A dermoscopy image of a single skin lesion.
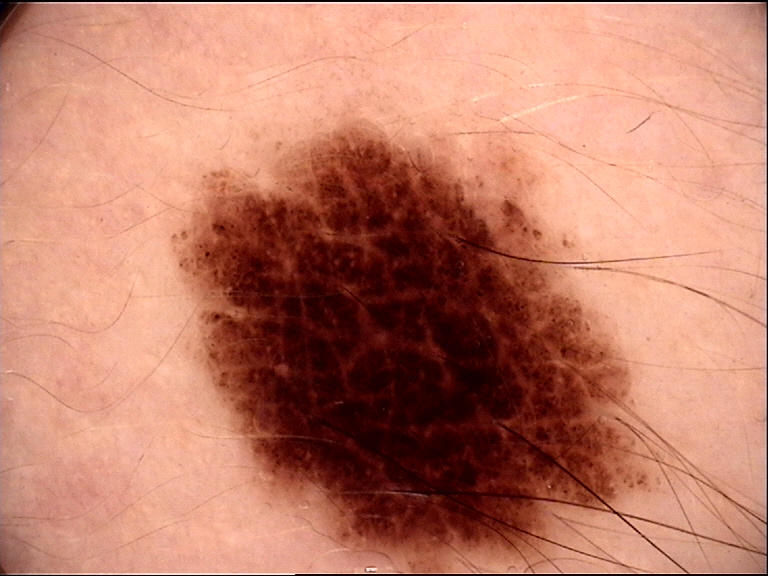Impression:
Labeled as a benign lesion — a dysplastic compound nevus.